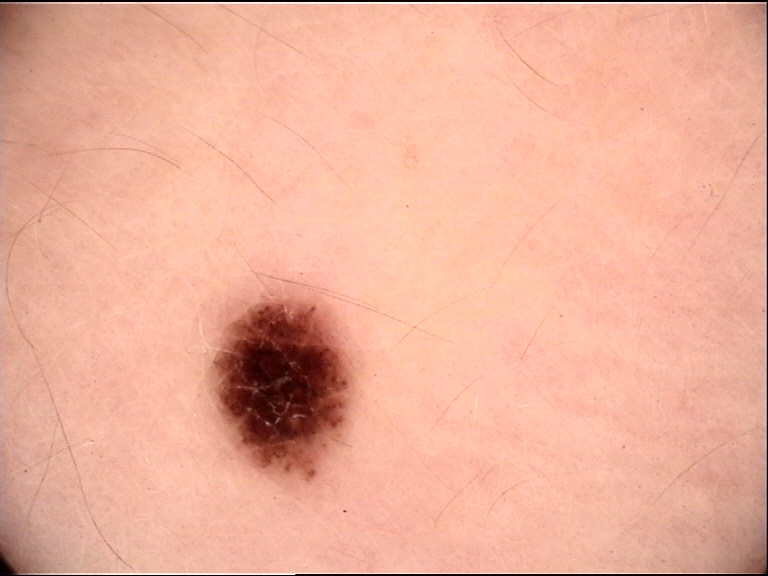Impression: Consistent with a dysplastic junctional nevus.